A skin lesion imaged with a dermatoscope.
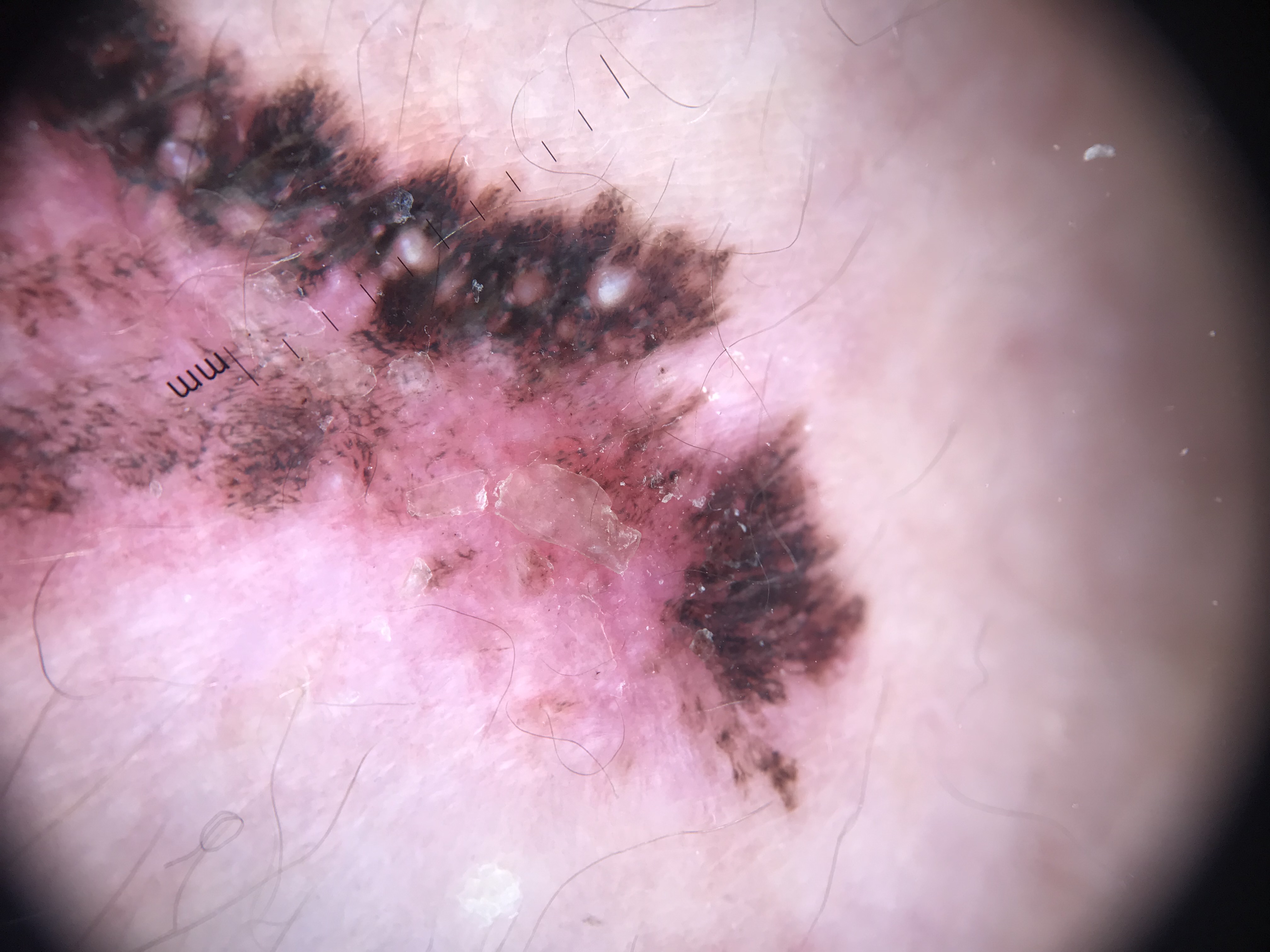Conclusion:
Histopathology confirmed a malignant lesion — a melanoma.